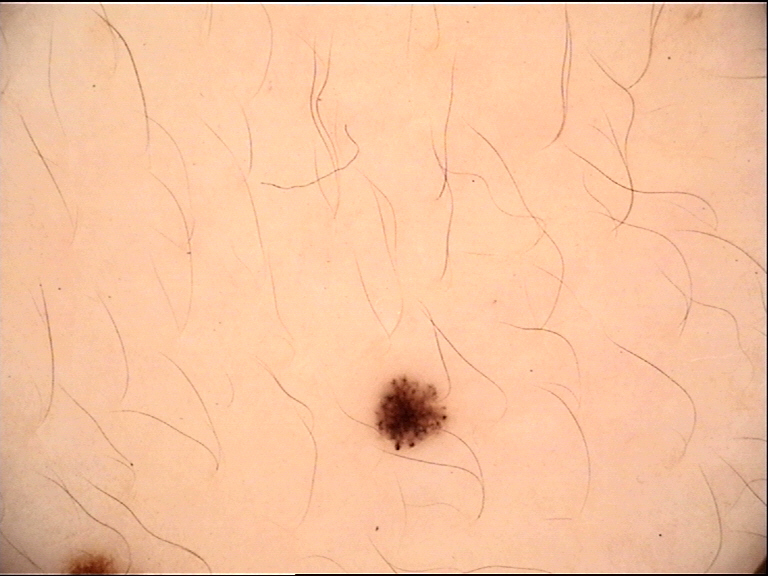The diagnostic label was a dysplastic junctional nevus.